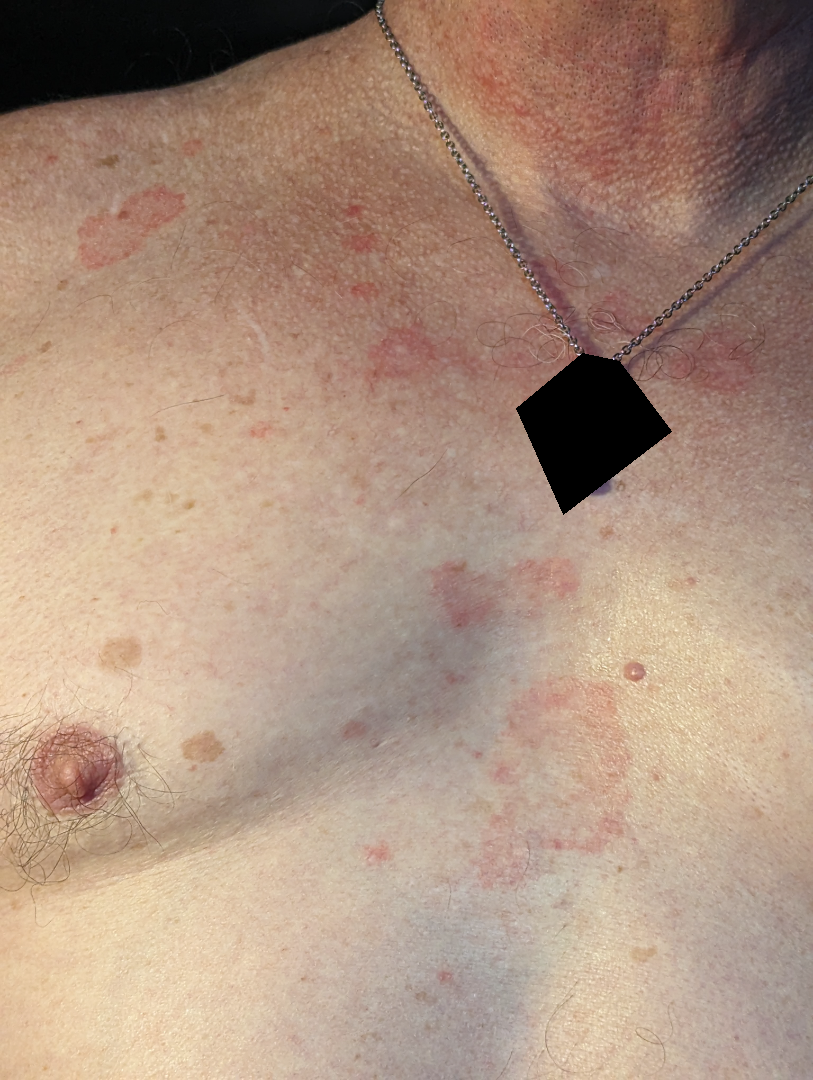| field | value |
|---|---|
| described texture | flat |
| site | head or neck, front of the torso and back of the torso |
| subject | male, age 50–59 |
| photo taken | close-up |
| patient's own categorization | a rash |
| associated systemic symptoms | chills |
| reported symptoms | bothersome appearance |
| clinical impression | consistent with Seborrheic Dermatitis |